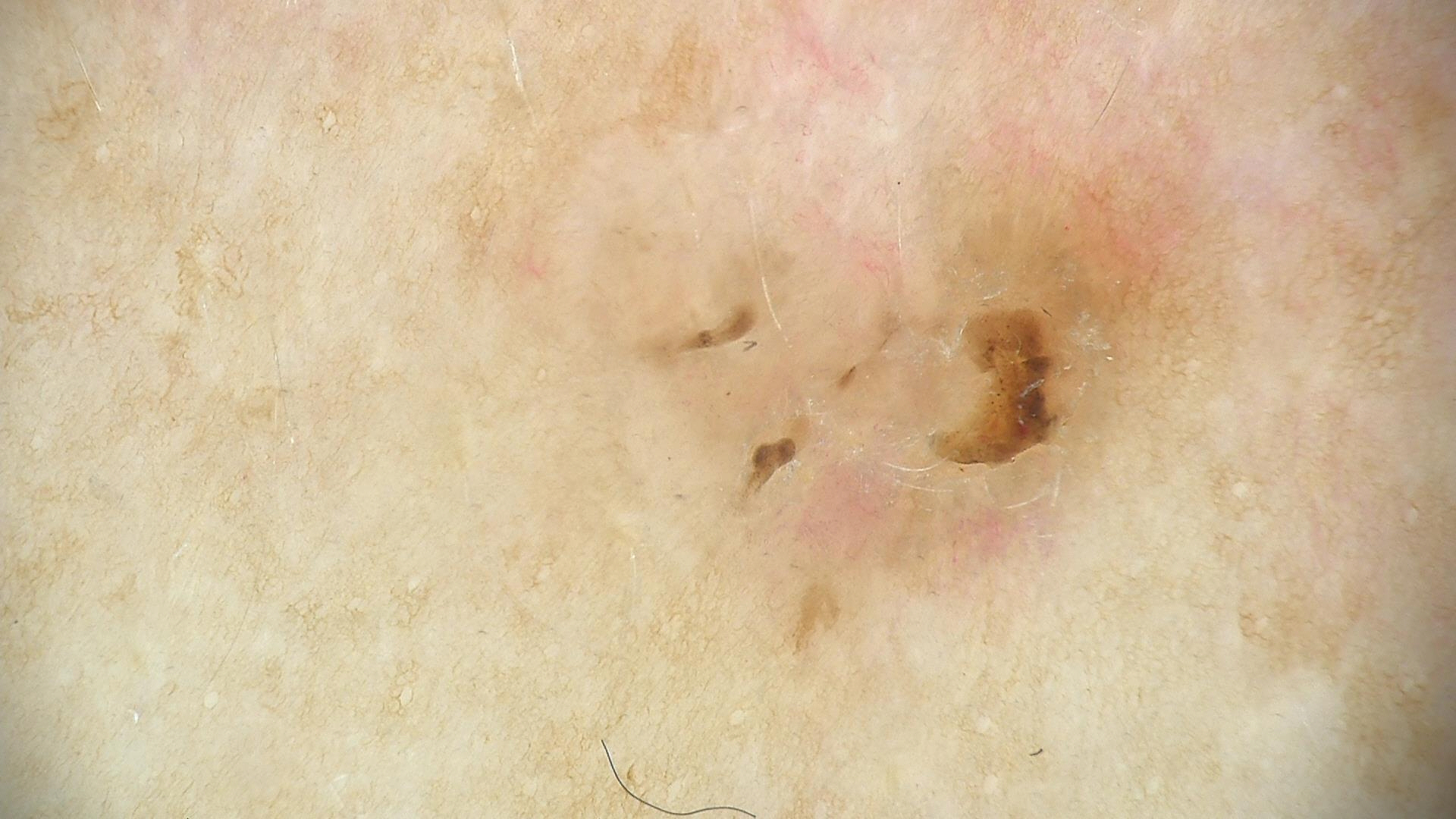A skin lesion imaged with a dermatoscope. The morphology is that of a keratinocytic lesion. Diagnosed as a seborrheic keratosis.